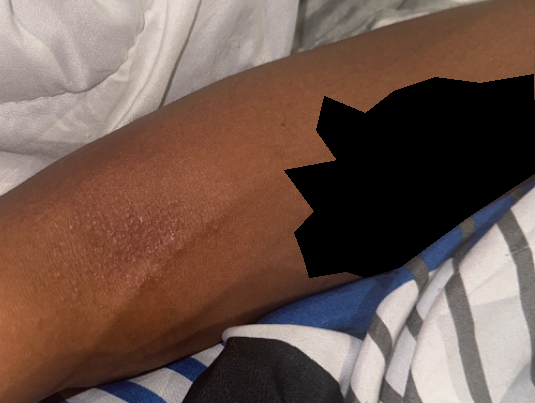subject — male, age 18–29 | anatomic site — arm | shot type — at a distance | clinical impression — Eczema (leading).